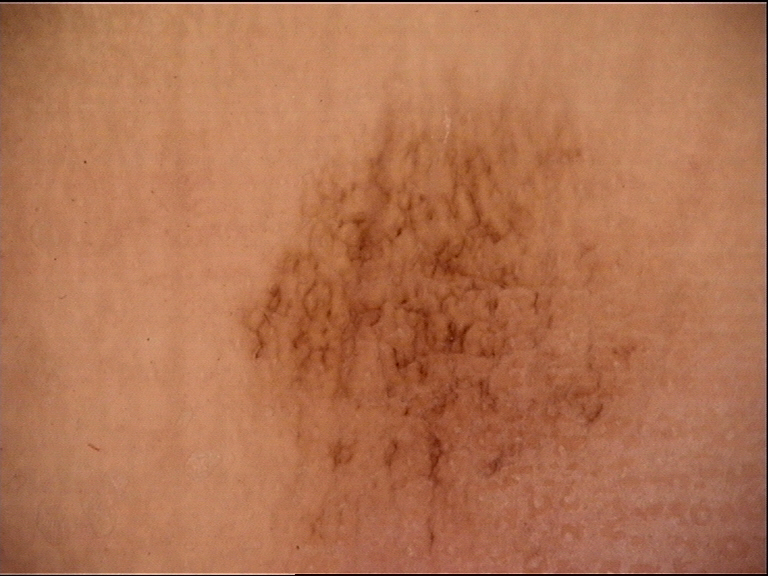Findings: A dermoscopic photograph of a skin lesion. Impression: Diagnosed as an acral dysplastic junctional nevus.